The photograph was taken at an angle; the affected area is the leg.
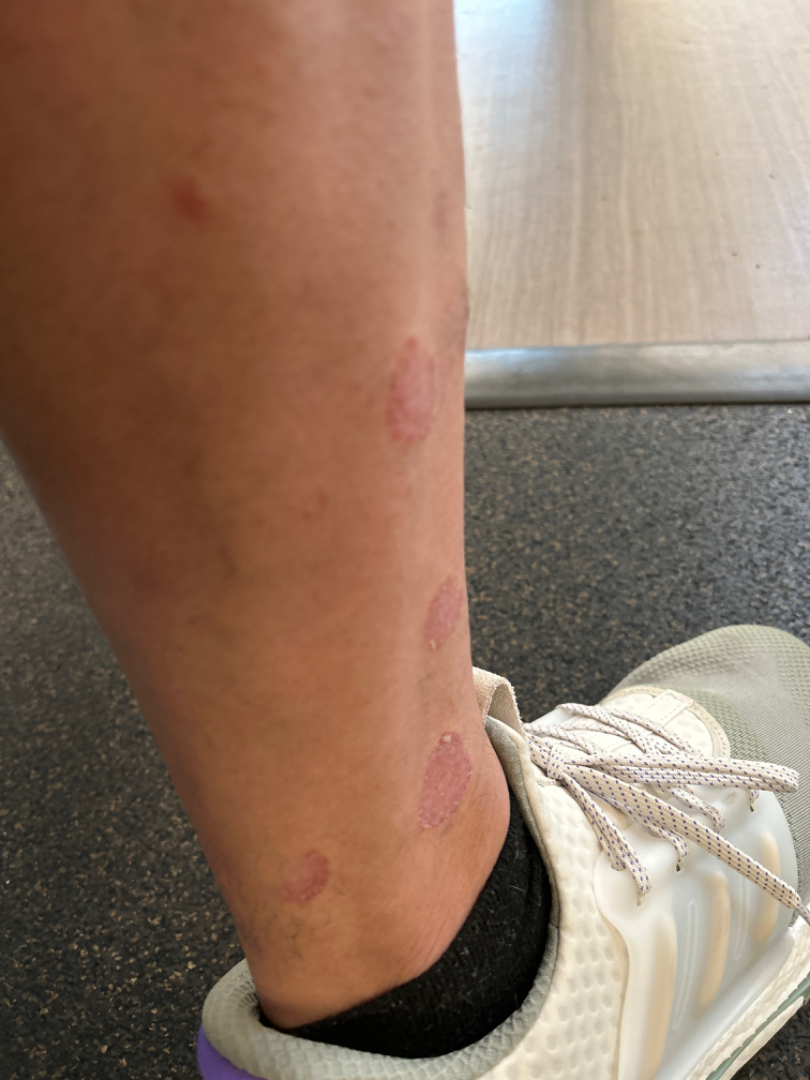The patient considered this a rash. The lesion is described as rough or flaky. The condition has been present for more than five years. The lesion is associated with bothersome appearance. Eczema (favored); Parapsoriasis (possible); Psoriasis (possible).